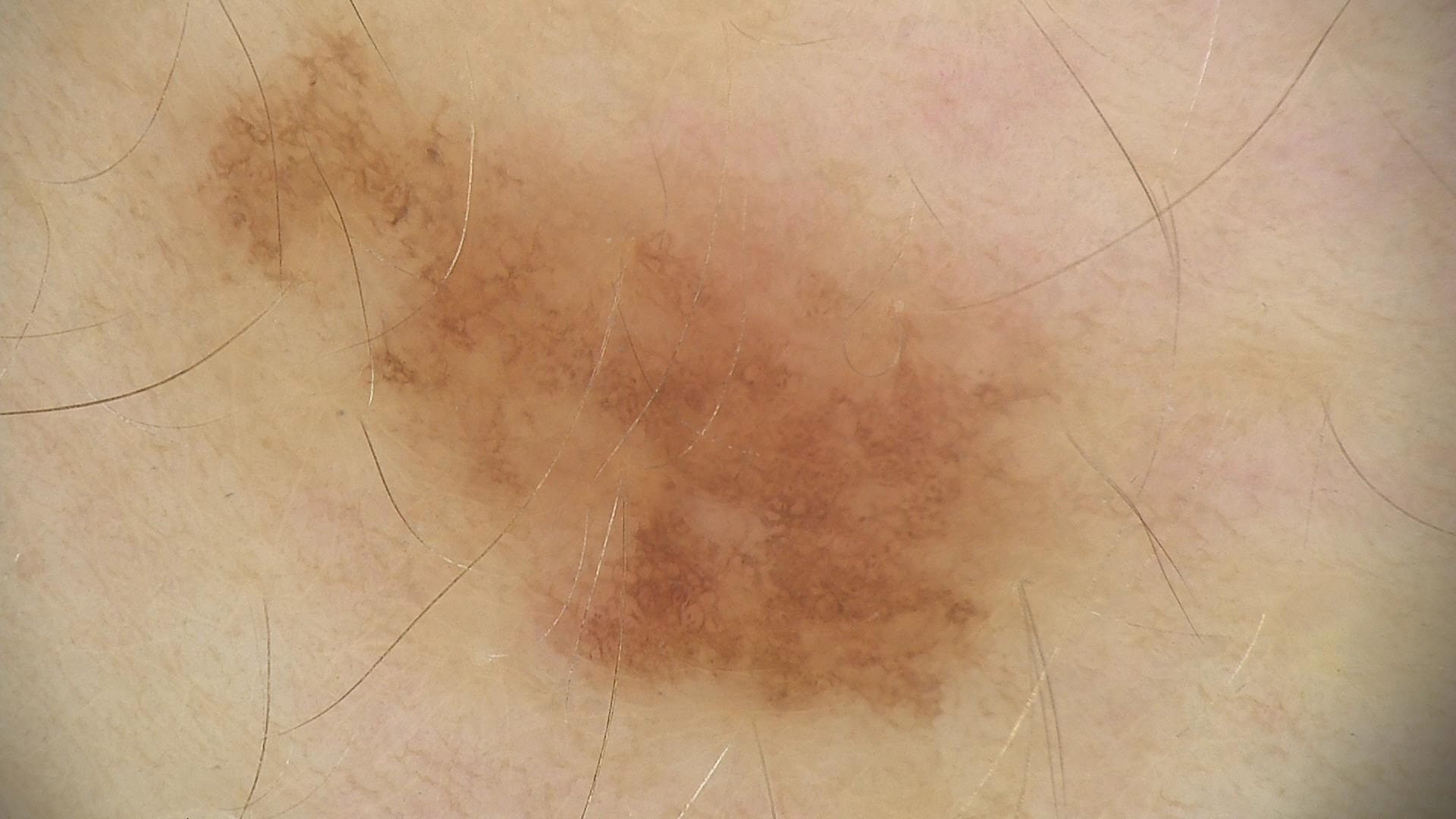Classified as a dysplastic junctional nevus.